Dermoscopy of a skin lesion.
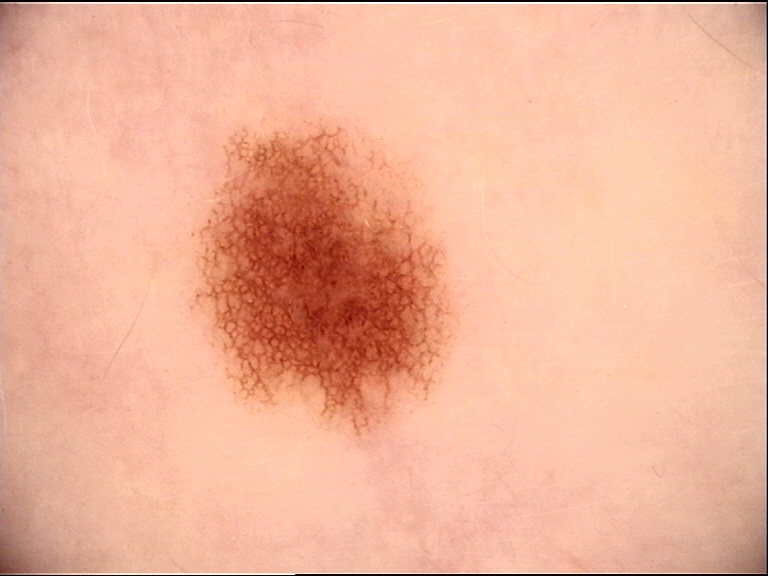Case:
- subtype: banal
- assessment: junctional nevus (expert consensus)